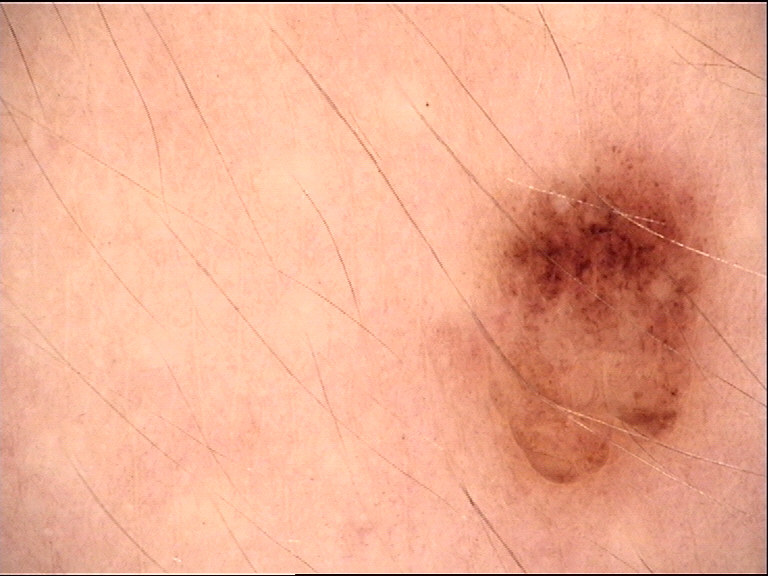Consistent with a banal lesion — a compound nevus.